A close-up photograph, reported duration is less than one week, reported lesion symptoms include itching, the patient described the issue as a rash, texture is reported as raised or bumpy, the subject is a male aged 60–69, the leg is involved: 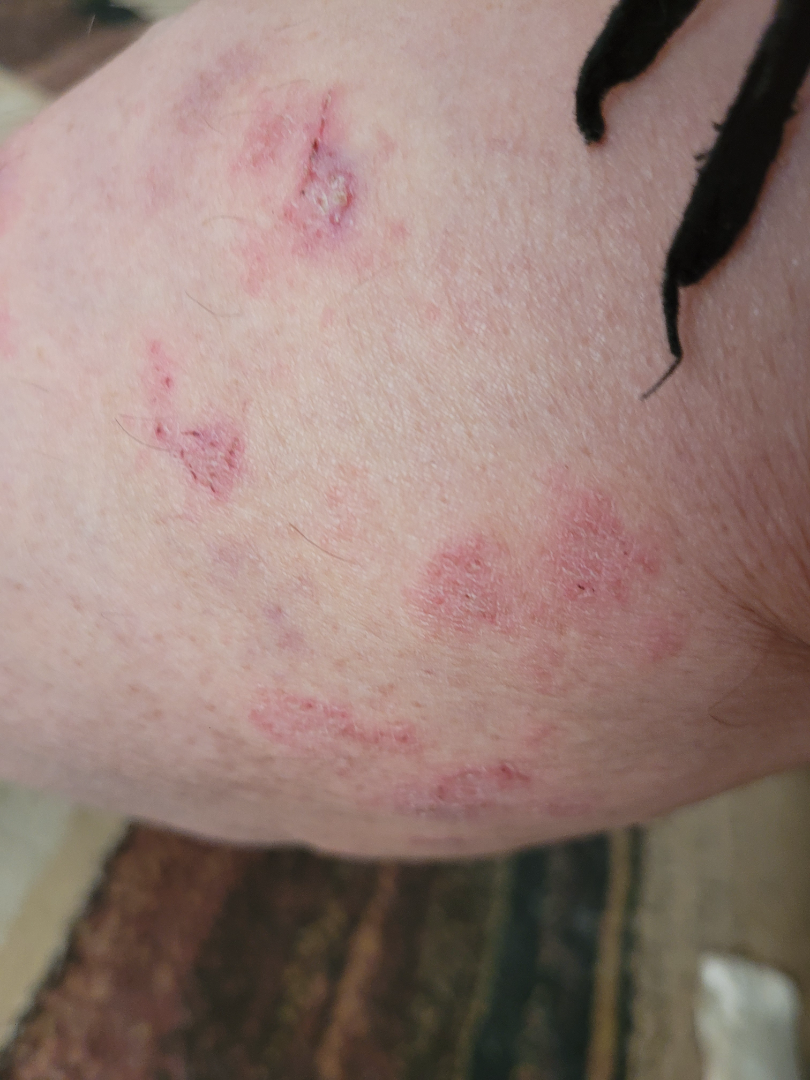{
  "differential": {
    "leading": [
      "Eczema"
    ],
    "considered": [
      "Pityriasis lichenoides"
    ]
  }
}